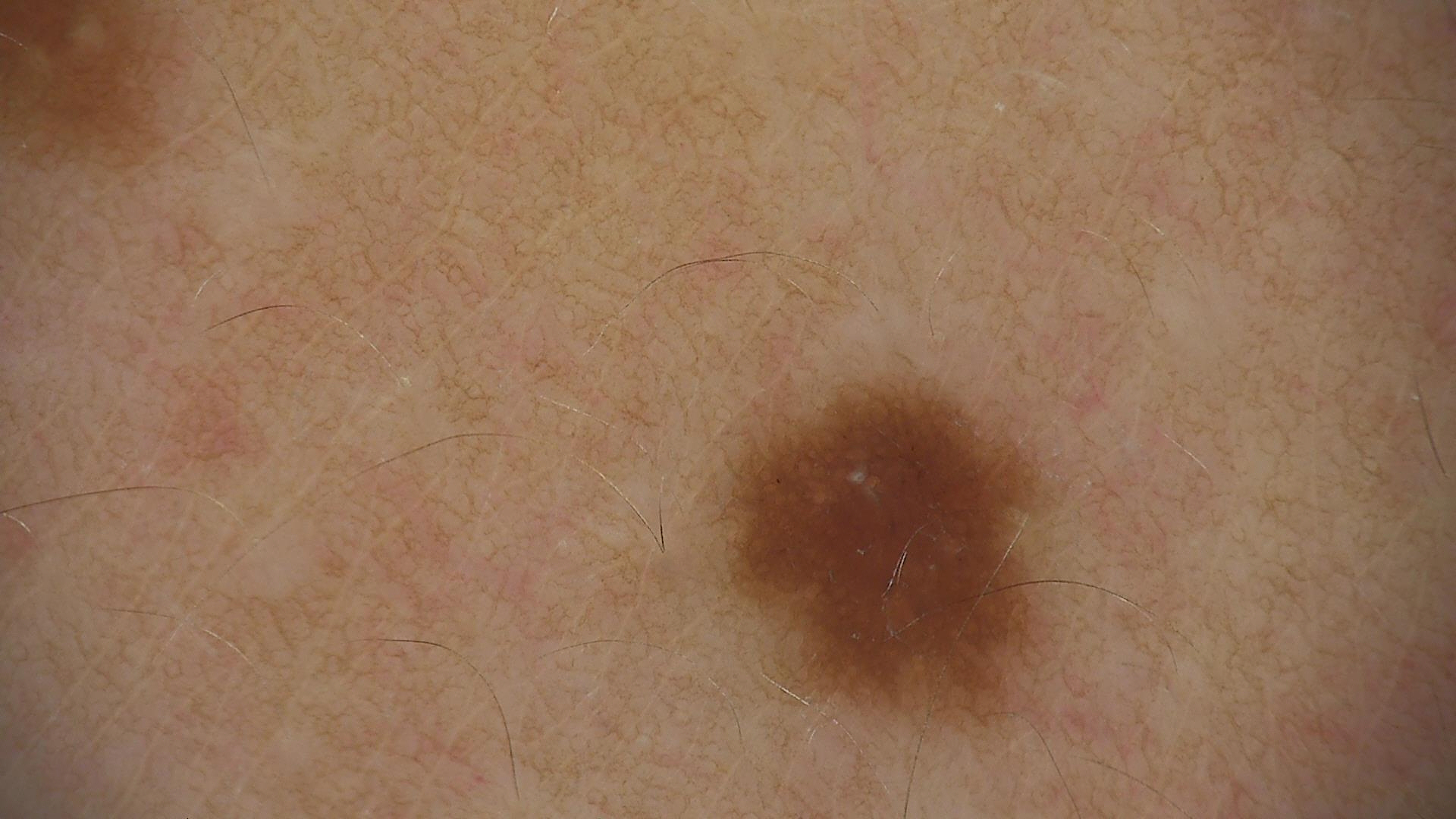A dermatoscopic image of a skin lesion. Classified as a benign lesion — a dysplastic junctional nevus.